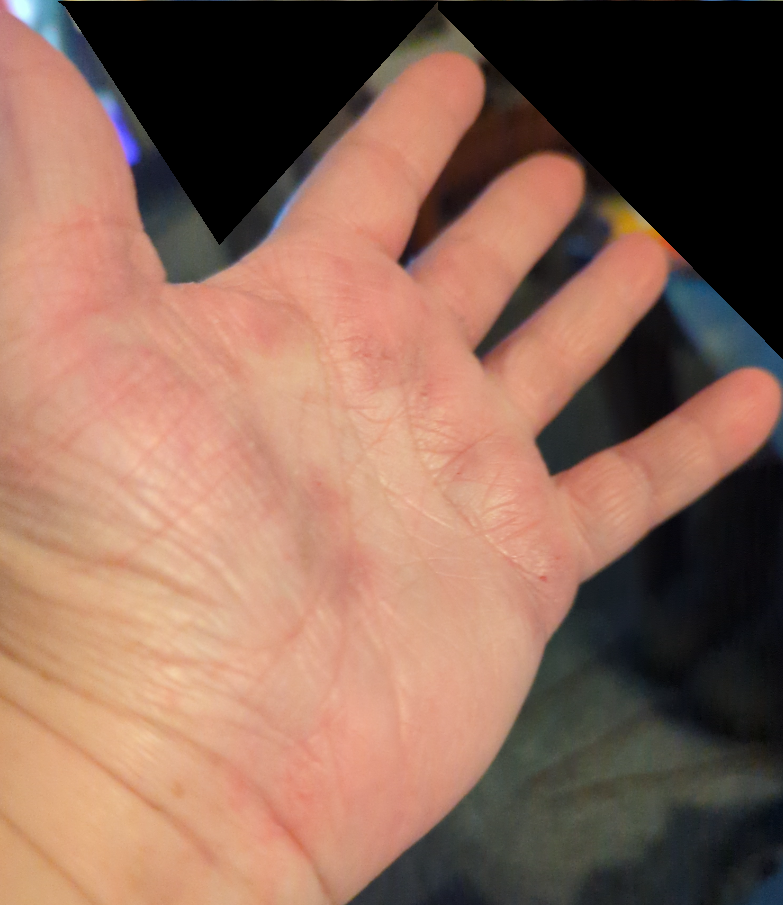assessment: in keeping with Eczema.